Female contributor, age 60–69 · a close-up photograph · the head or neck, front of the torso and back of the torso are involved: 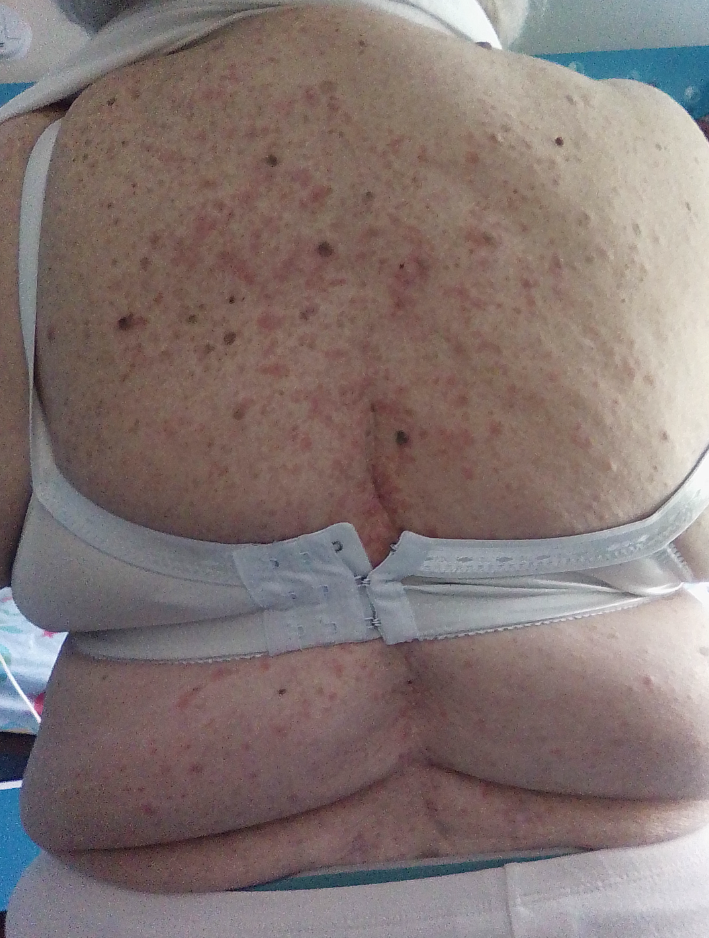The reviewing clinician's impression was: Drug Rash (possible); Eczema (possible); Hypersensitivity (possible).